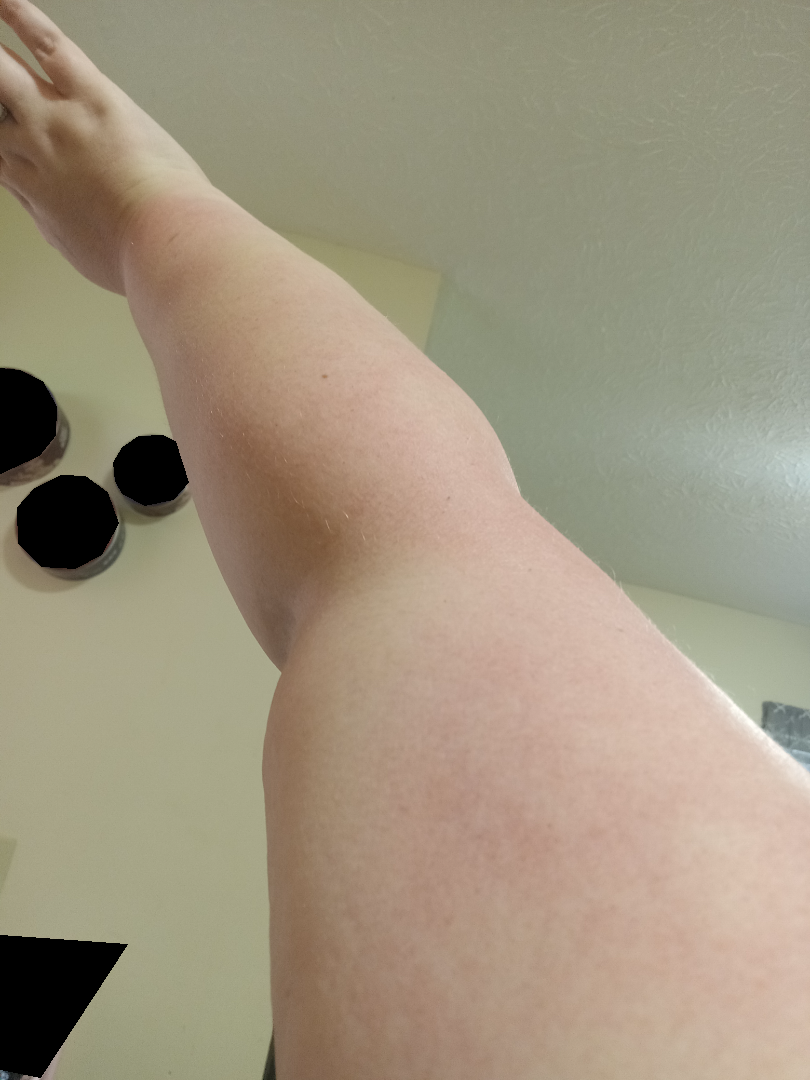assessment — no clear pathology | systemic symptoms — fatigue, joint pain and chills | patient-reported symptoms — burning | image framing — at a distance | self-categorized as — a rash | duration — about one day | site — arm, back of the hand and head or neck | skin tone — Fitzpatrick II; human graders estimated Monk skin tone scale 1 | described texture — raised or bumpy and flat | contributor — female, age 30–39.